The photograph was taken at a distance. Located on the arm. Present for less than one week. The contributor reports the lesion is flat:
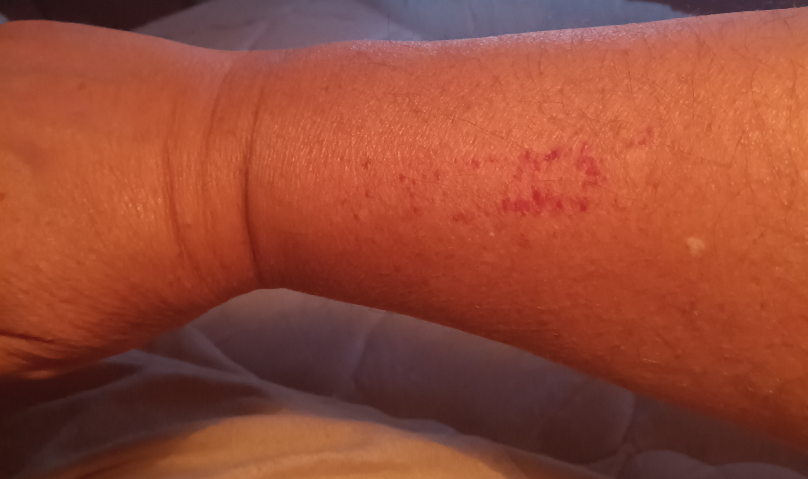<case>
  <assessment>not assessable</assessment>
</case>